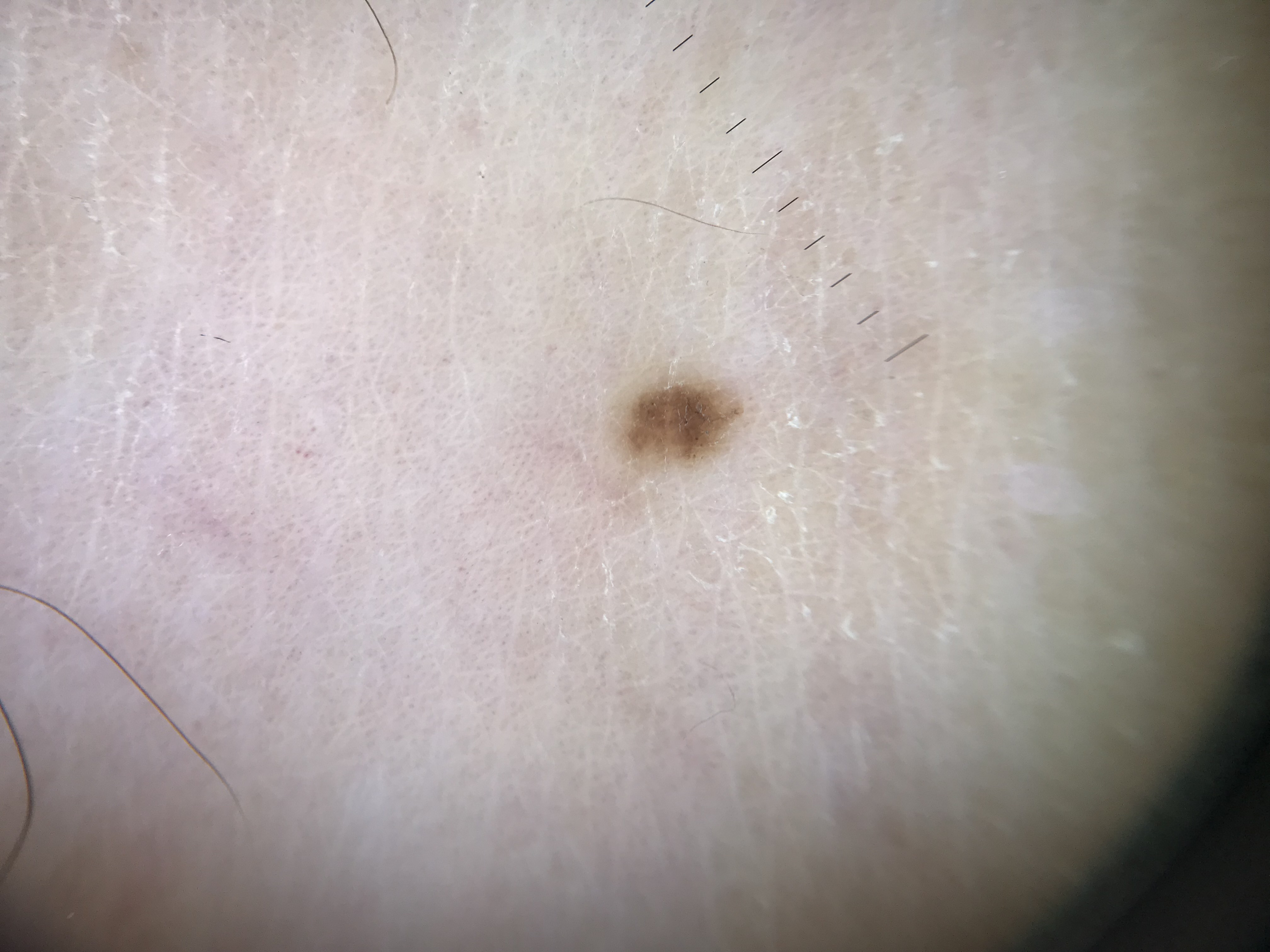Labeled as an acral junctional nevus.